The contributor is 18–29, female · this image was taken at a distance · self-categorized by the patient as a rash · the patient notes the lesion is rough or flaky and raised or bumpy · located on the head or neck and leg: 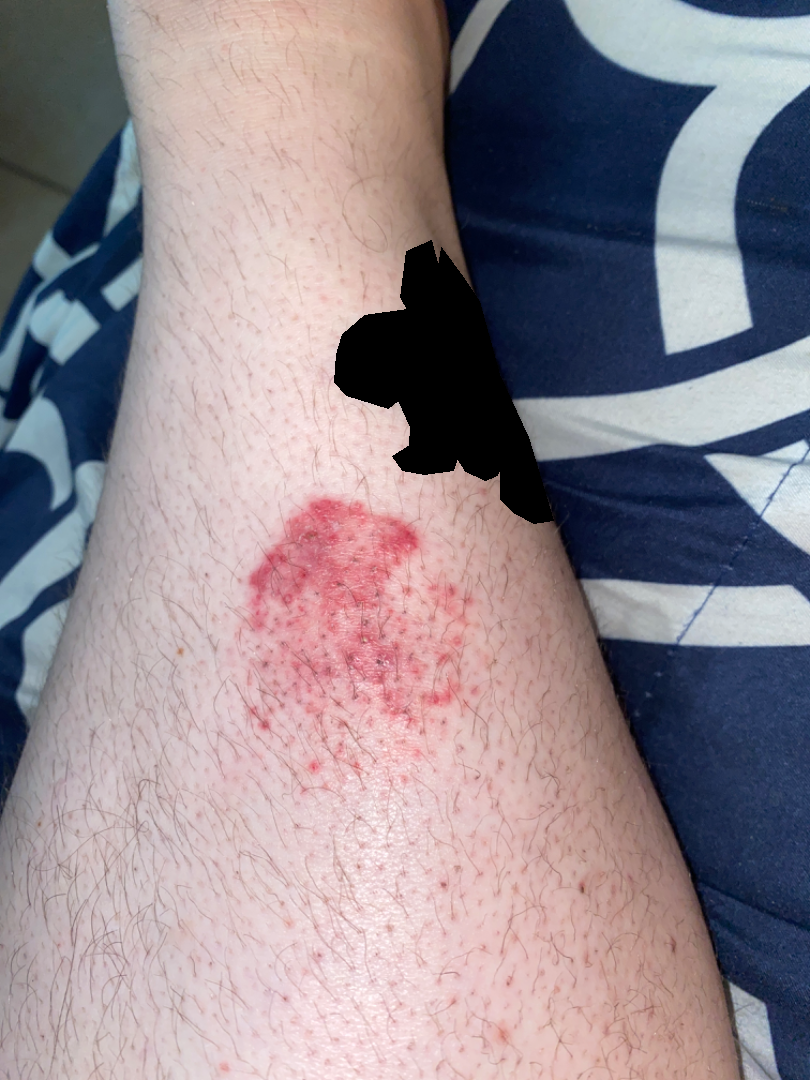Assessment:
Acute dermatitis, NOS (1.00).